Close-up view:
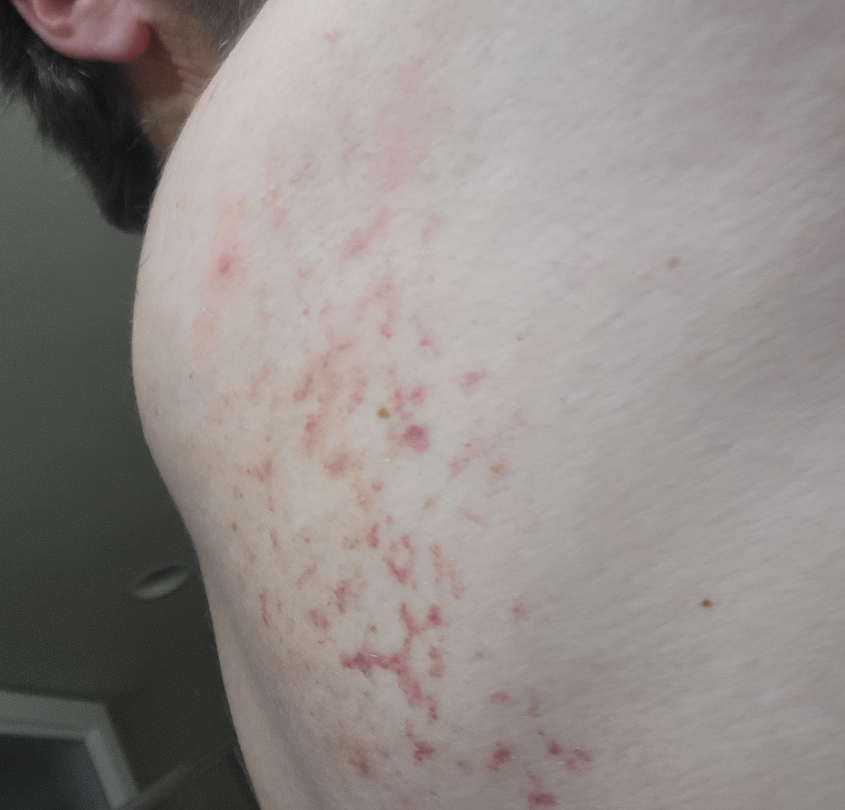The image was not sufficient for the reviewer to characterize the skin condition.
Fitzpatrick II.
The lesion is associated with bothersome appearance.
The lesion is described as flat.